A dermoscopic photograph of a skin lesion:
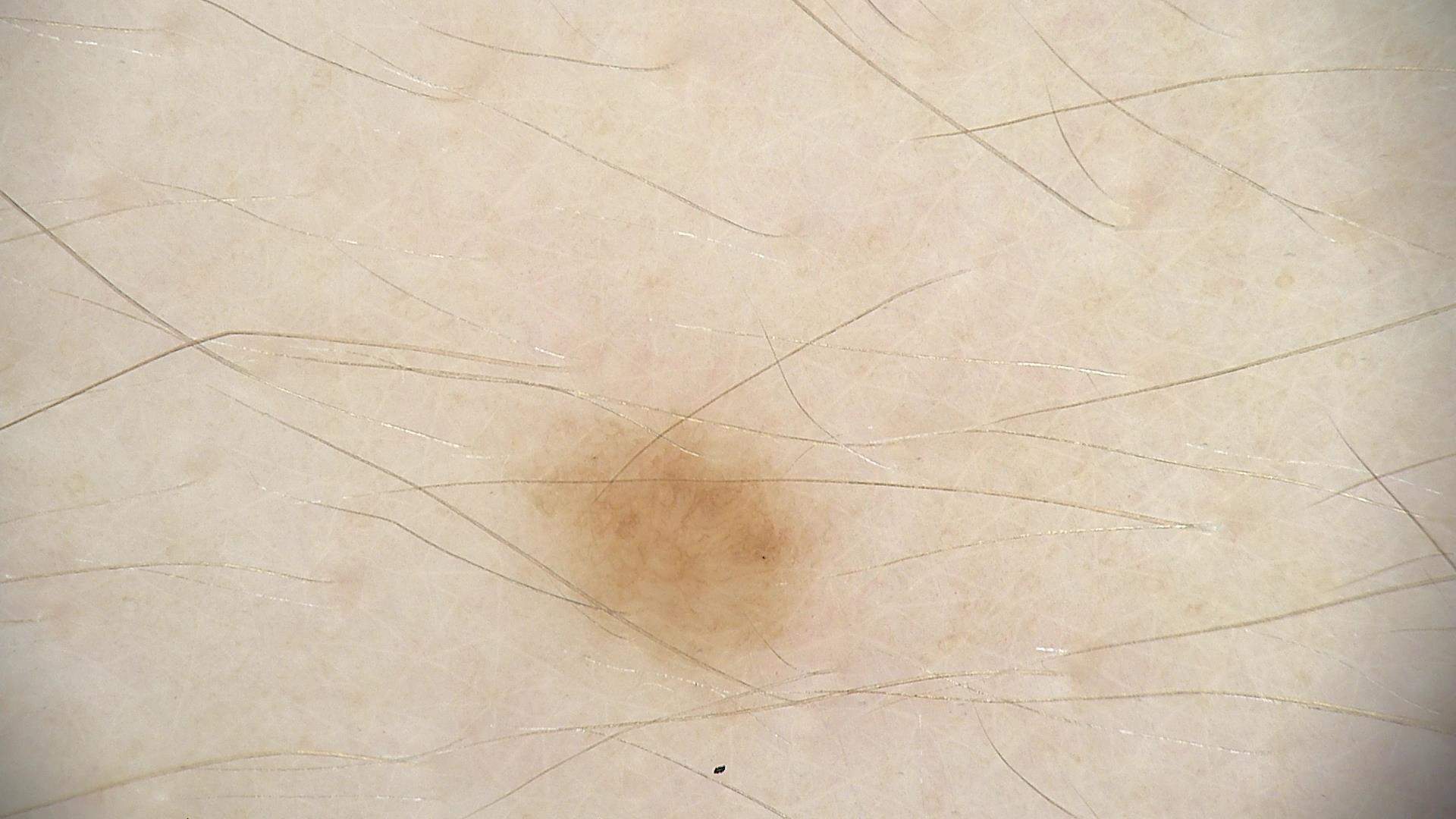The diagnosis was a dysplastic junctional nevus.